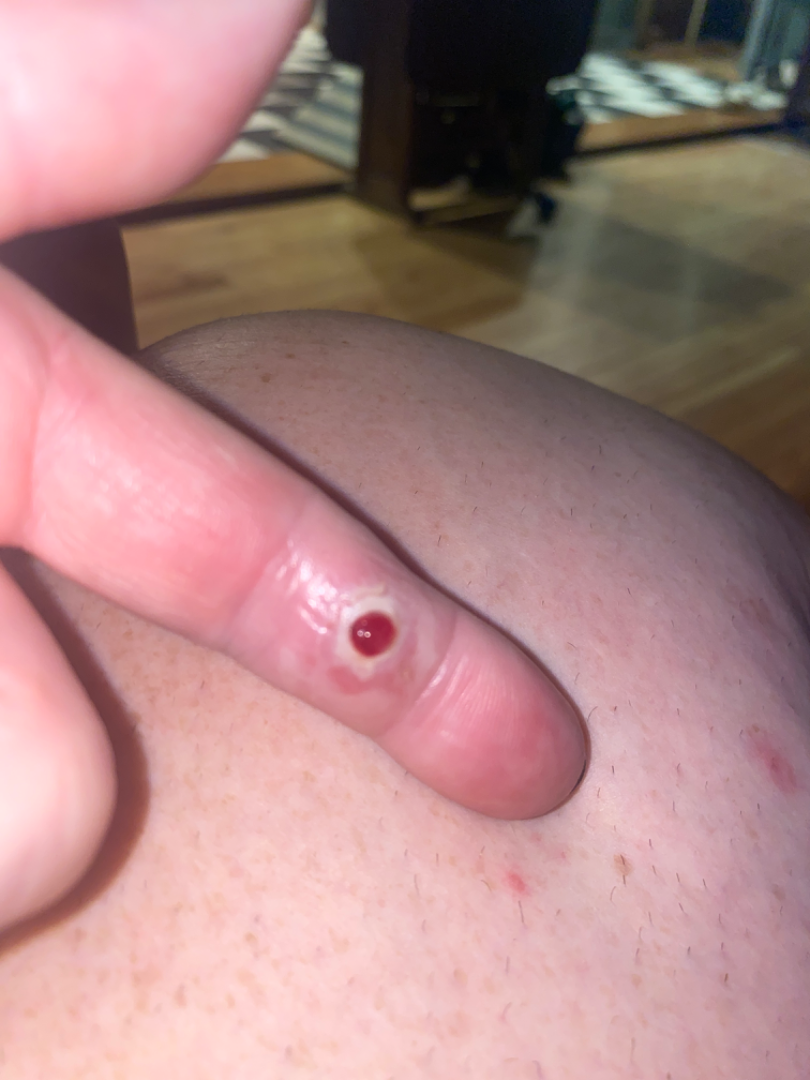dermatologist impression = the favored diagnosis is Pyogenic granuloma; also on the differential is Melanoma.